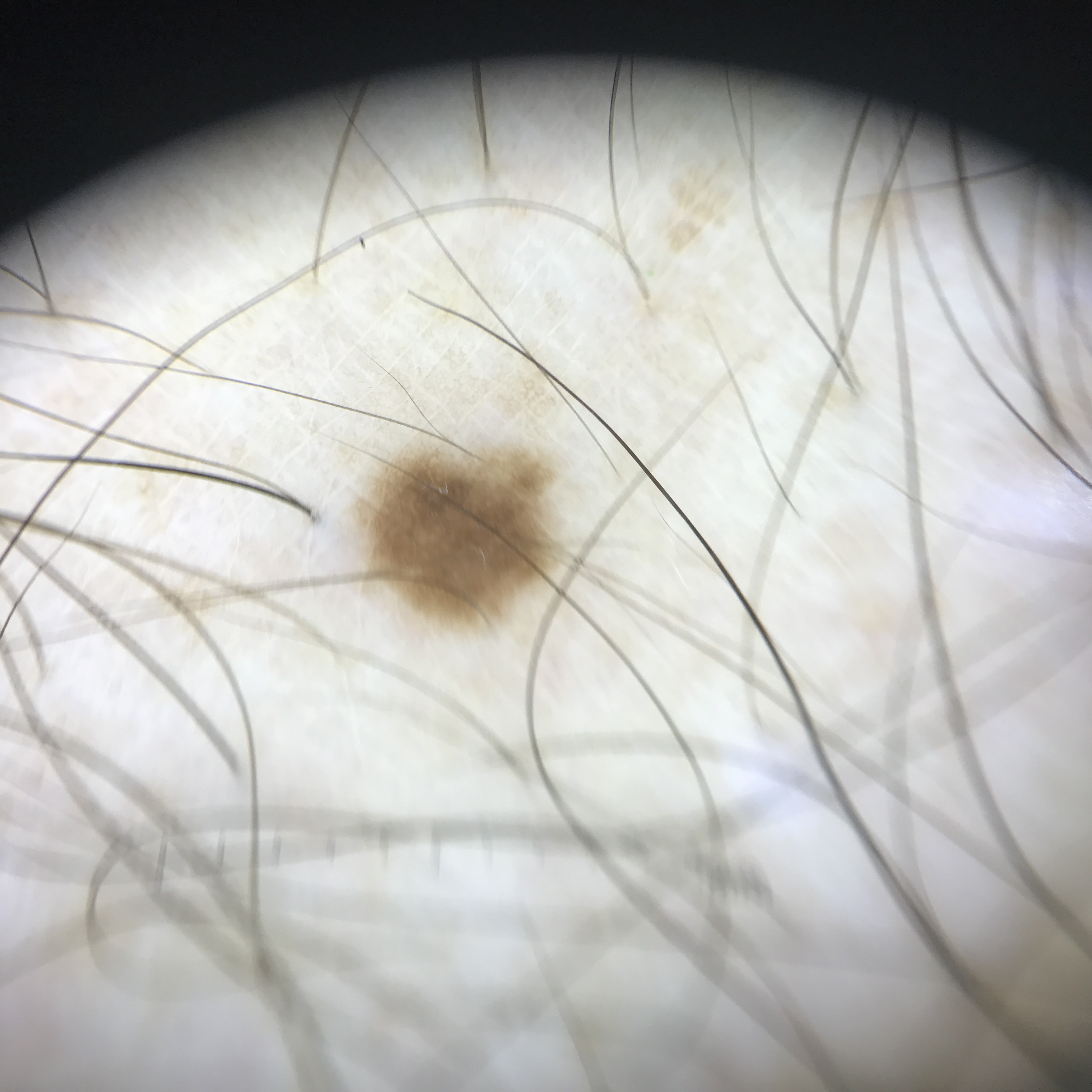imaging=dermoscopy
classification=banal
label=junctional nevus (expert consensus)